The photo was captured at an angle: 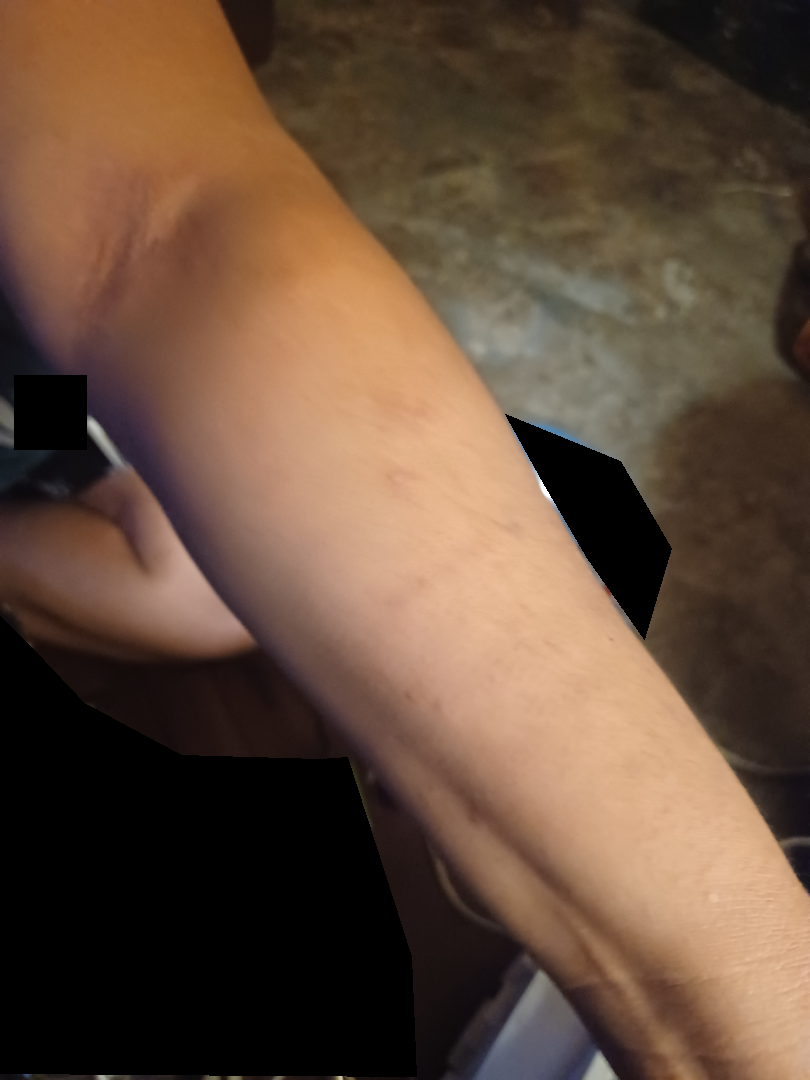assessment: indeterminate from the photograph.